A dermoscopic close-up of a skin lesion.
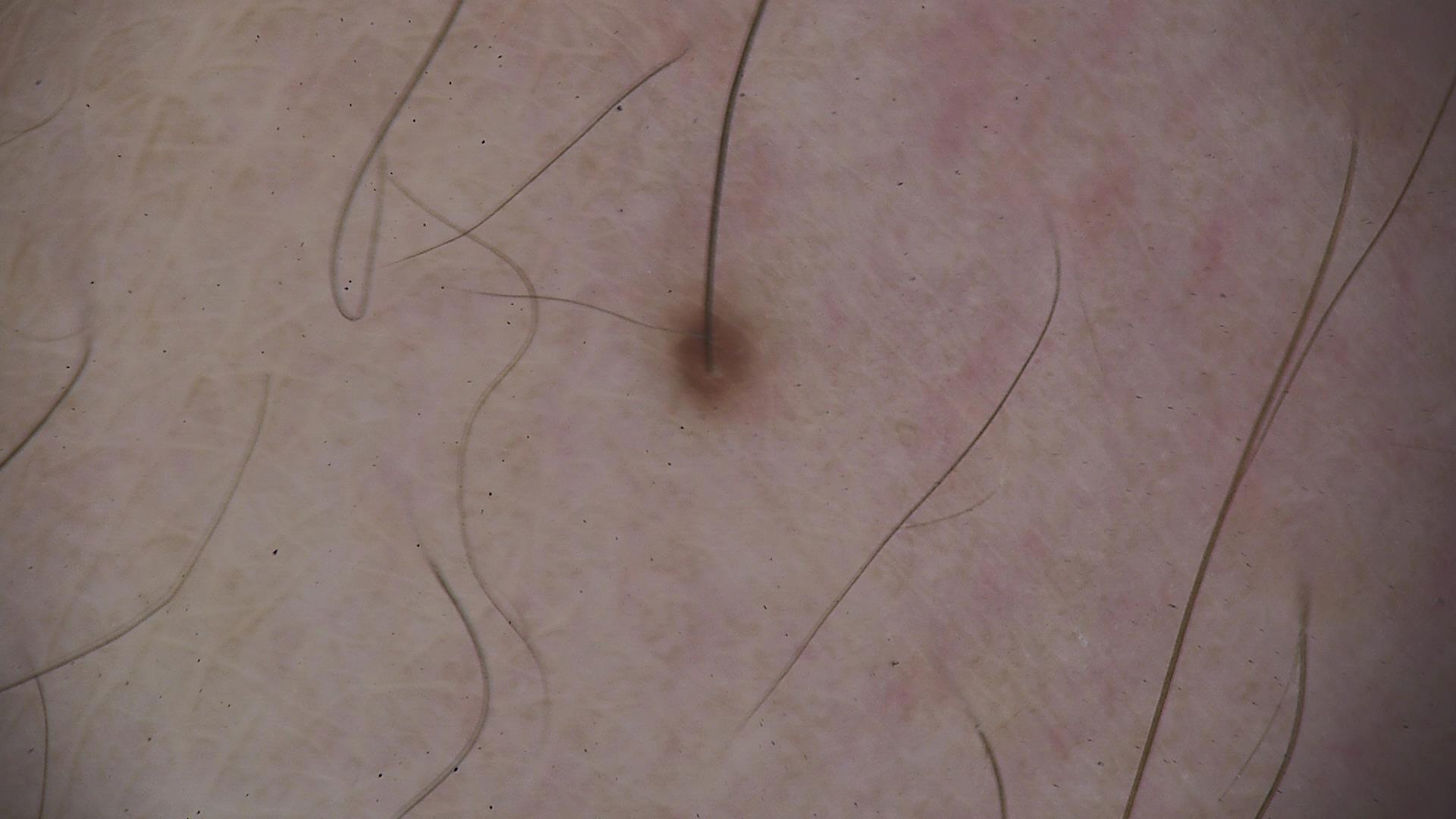Q: What was the diagnostic impression?
A: junctional nevus (expert consensus)